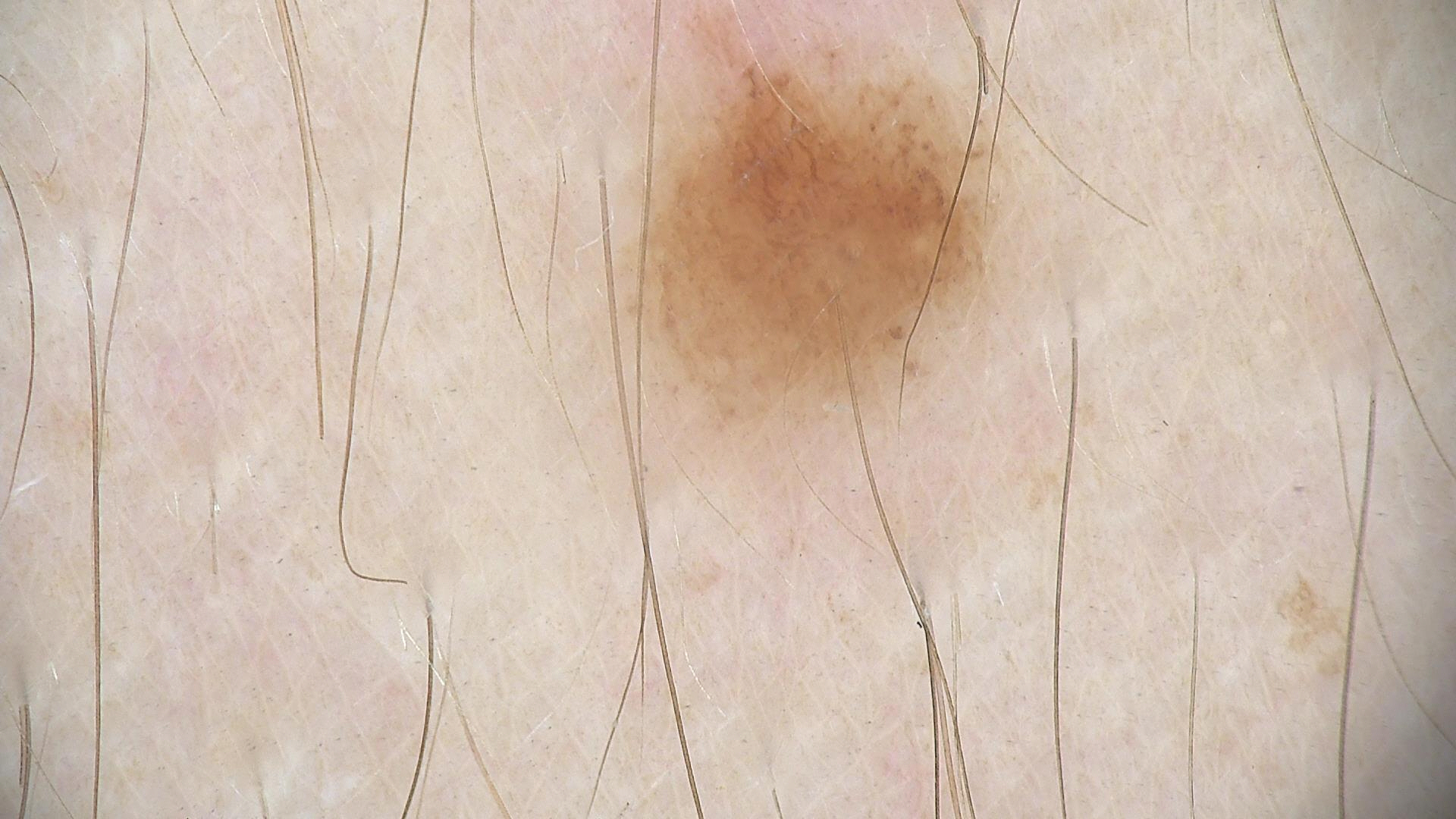Q: What is the imaging modality?
A: dermoscopy
Q: What is this lesion?
A: dysplastic junctional nevus (expert consensus)